A male patient 89 years of age · a skin lesion imaged with a dermatoscope — 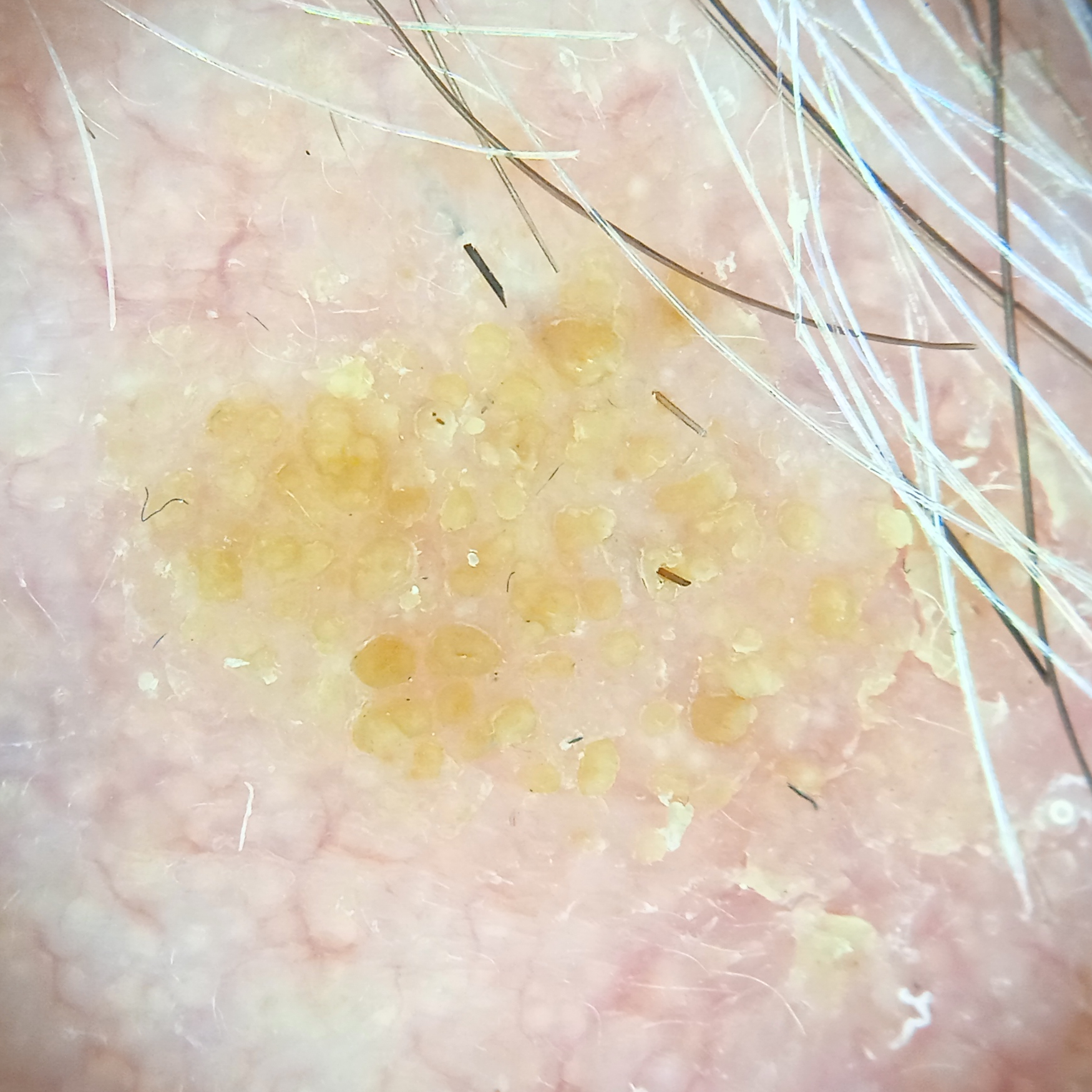The lesion involves the face. The lesion measures approximately 8.8 mm. The dermatologists' assessment was a seborrheic keratosis.